This is a dermoscopic photograph of a skin lesion: 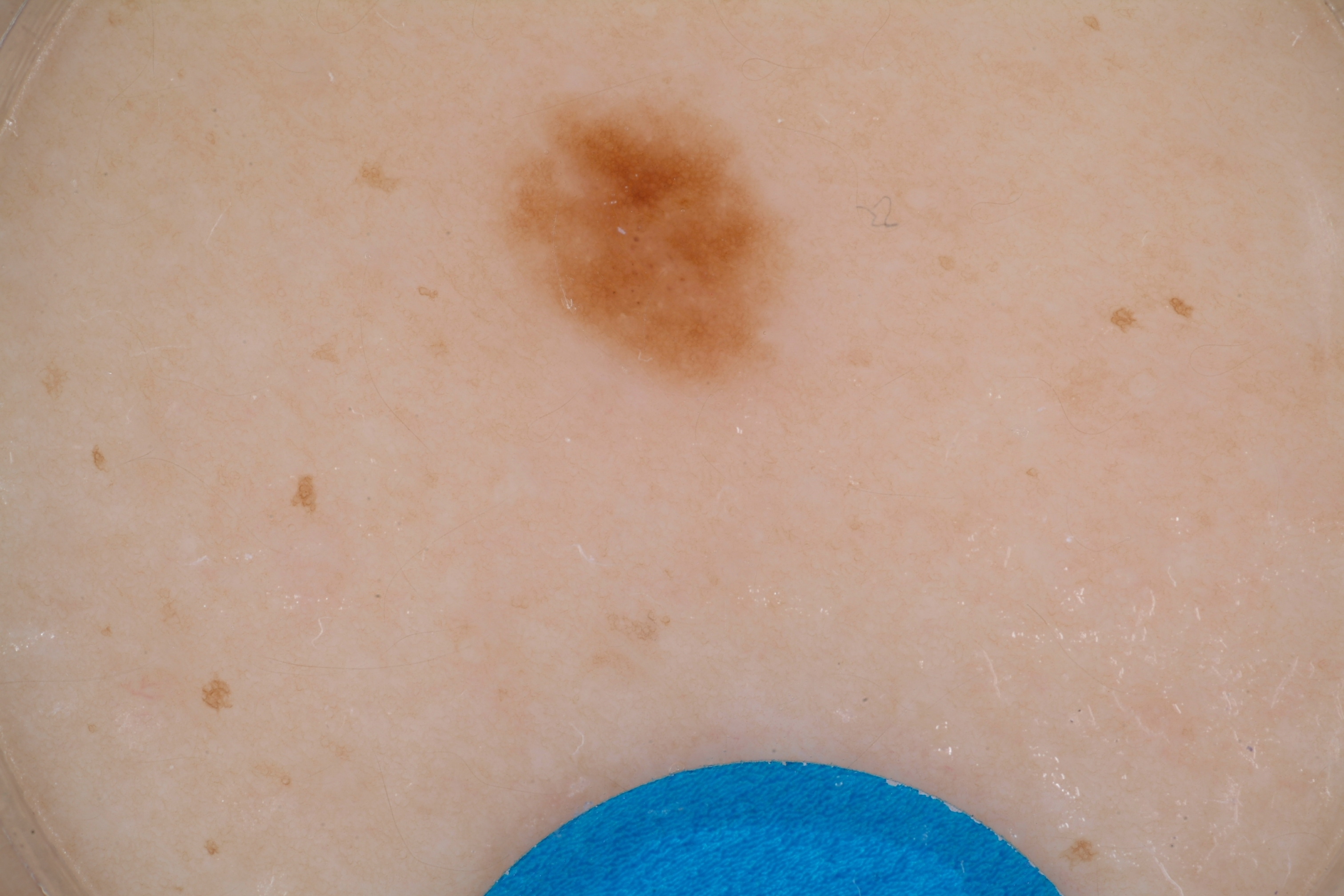| key | value |
|---|---|
| lesion size | ~6% of the field |
| dermoscopic findings | globules; absent: streaks |
| location | bbox(481, 62, 798, 399) |
| assessment | a benign skin lesion |